A dermoscopic close-up of a skin lesion.
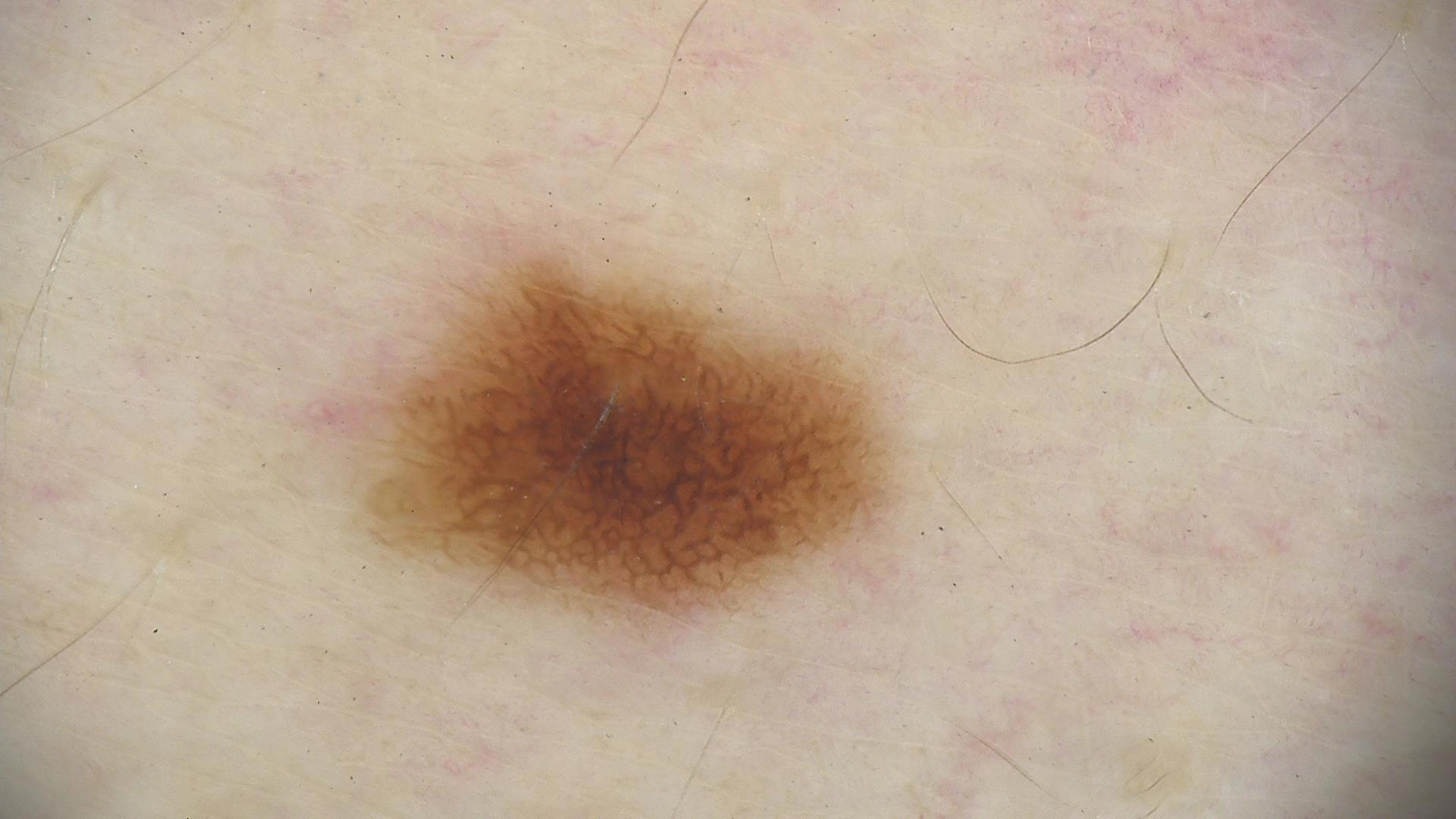The diagnosis was a benign lesion — a dysplastic junctional nevus.